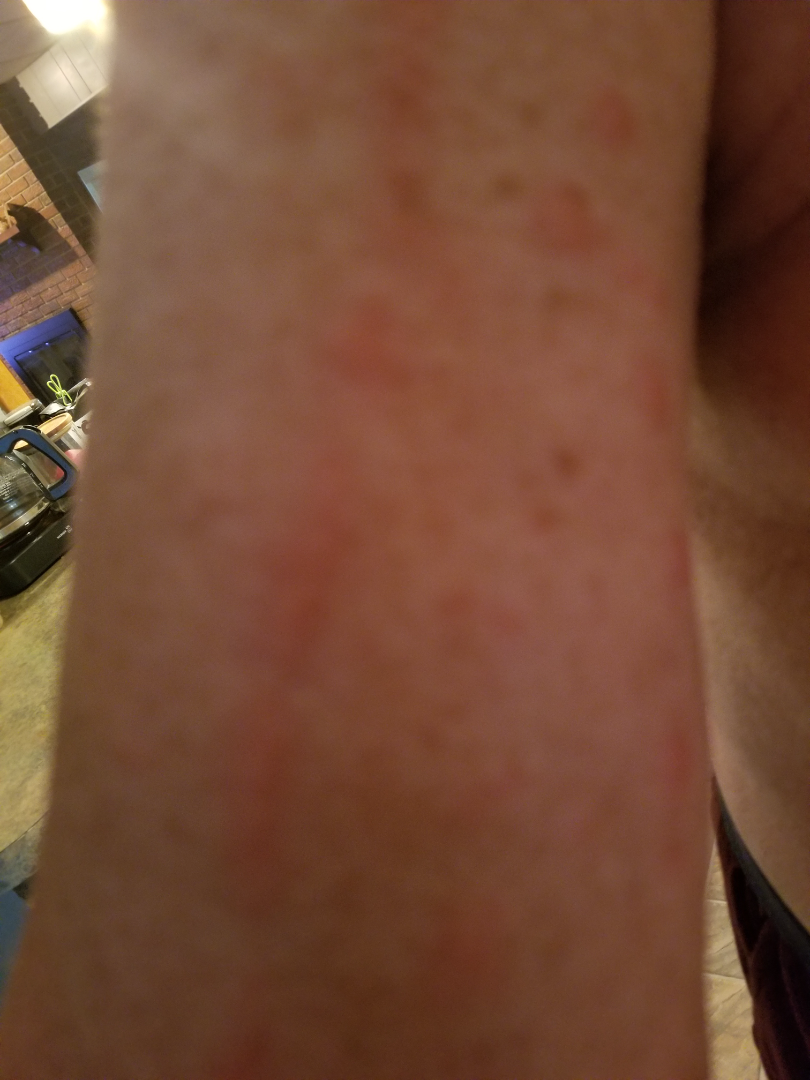Case summary:
* subject: male, age 70–79
* affected area: arm and front of the torso
* described texture: raised or bumpy and rough or flaky
* skin tone: lay reviewers estimated Monk Skin Tone 6 (US pool) or 2 (India pool)
* shot type: close-up
* duration: less than one week
* patient describes the issue as: a rash
* patient-reported symptoms: bothersome appearance and itching
* clinical impression: Eczema (possible); Allergic Contact Dermatitis (possible)